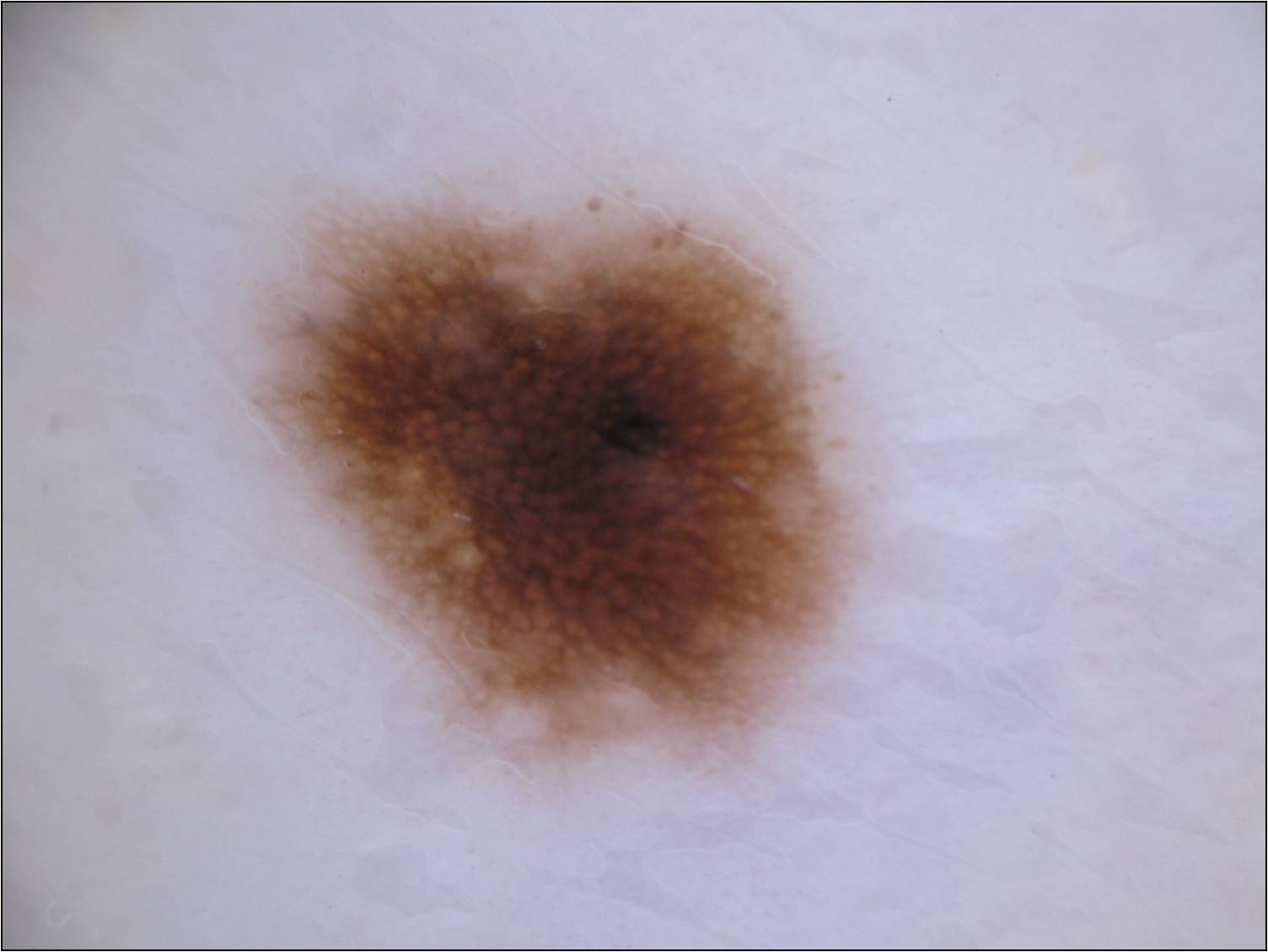<lesion>
  <image>
    <modality>dermoscopy</modality>
  </image>
  <dermoscopic_features>
    <present>pigment network, globules</present>
    <absent>negative network, streaks, milia-like cysts</absent>
  </dermoscopic_features>
  <lesion_location>
    <bbox_xyxy>216, 169, 873, 782</bbox_xyxy>
  </lesion_location>
  <diagnosis>
    <name>melanocytic nevus</name>
    <malignancy>benign</malignancy>
    <lineage>melanocytic</lineage>
    <provenance>clinical</provenance>
  </diagnosis>
</lesion>